The leg, arm, back of the torso and front of the torso are involved. This image was taken at an angle: 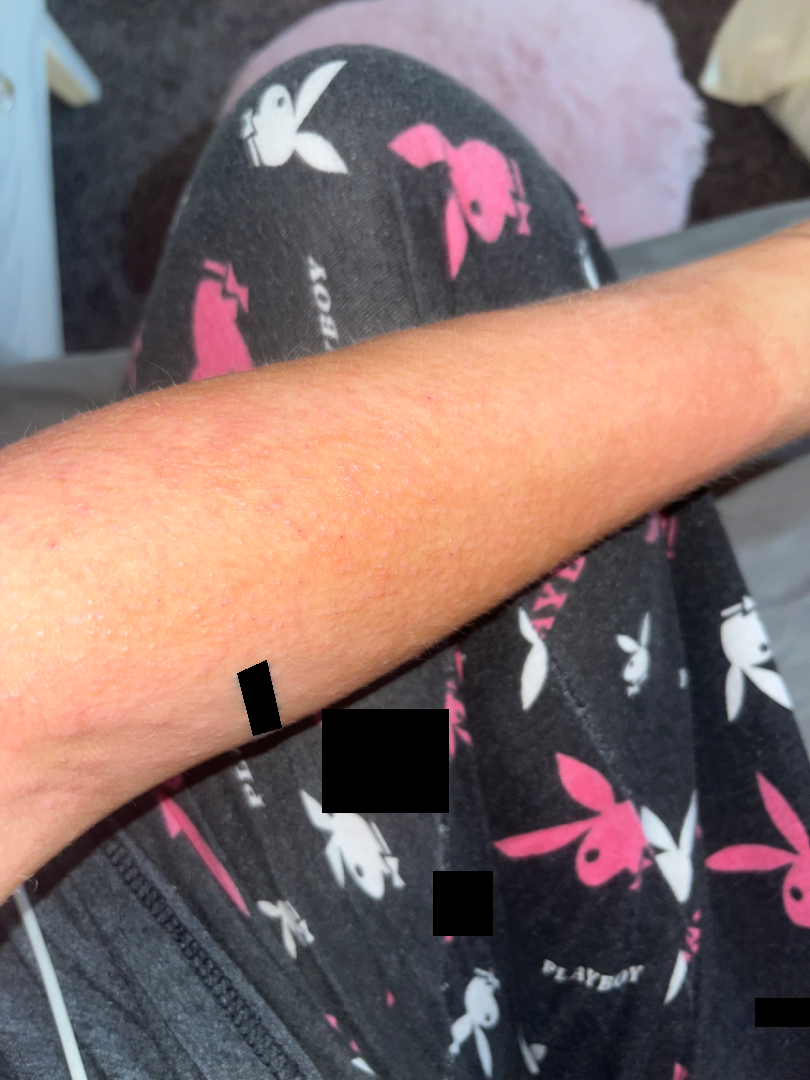Assessment: The condition could not be reliably identified from the image. Clinical context: Associated systemic symptoms include fever, fatigue and shortness of breath. Self-categorized by the patient as a rash. The condition has been present for one to three months. The lesion is associated with enlargement, itching and burning.